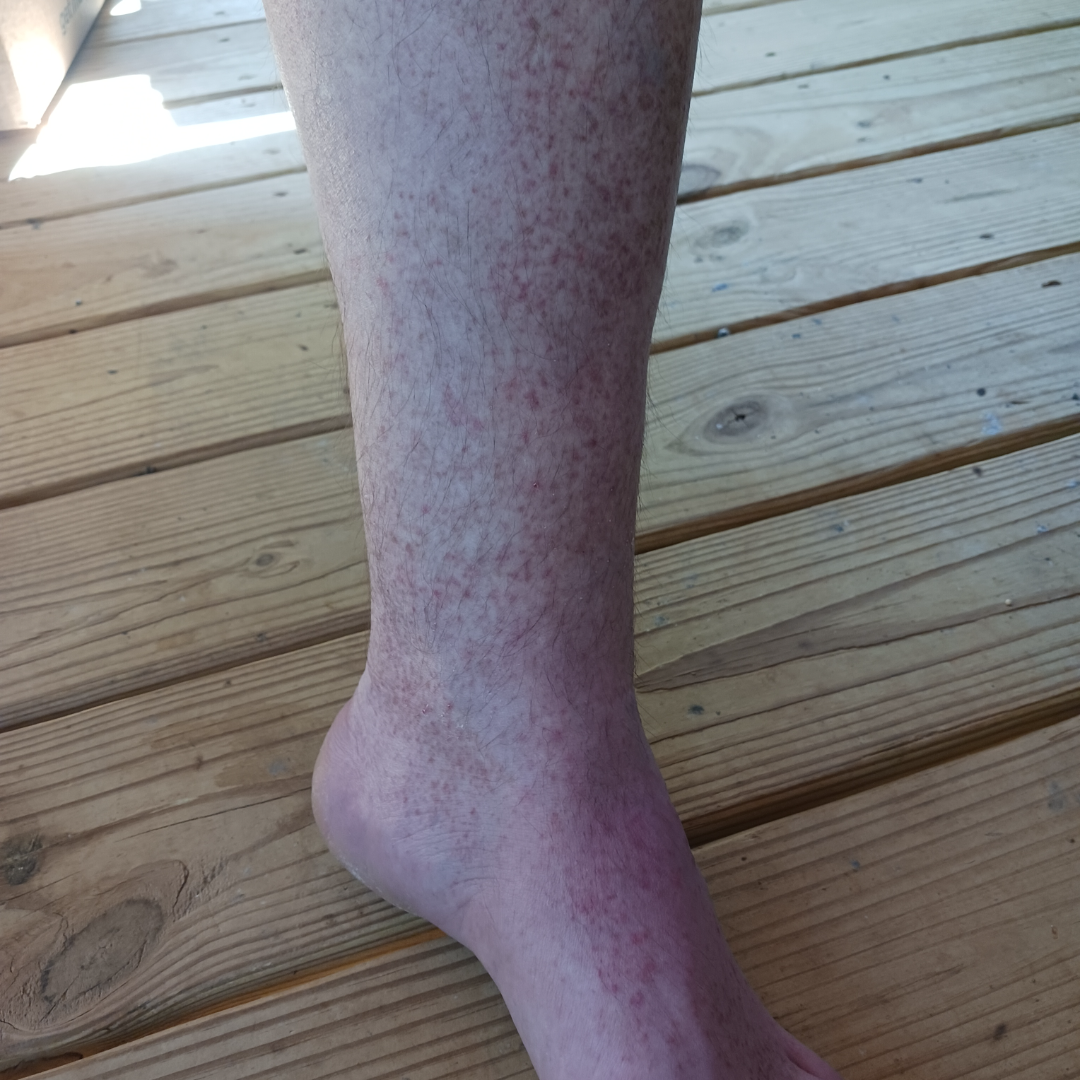Clinical context:
The top or side of the foot and leg are involved. An image taken at a distance. The patient reported no systemic symptoms. The lesion is described as raised or bumpy. Self-categorized by the patient as a rash. Reported lesion symptoms include bothersome appearance, darkening, itching and pain.
Assessment:
On photographic review by a dermatologist: Pigmented purpuric eruption, Allergic Contact Dermatitis and Leukocytoclastic Vasculitis were each considered, in no particular order.